A dermatoscopic image of a skin lesion:
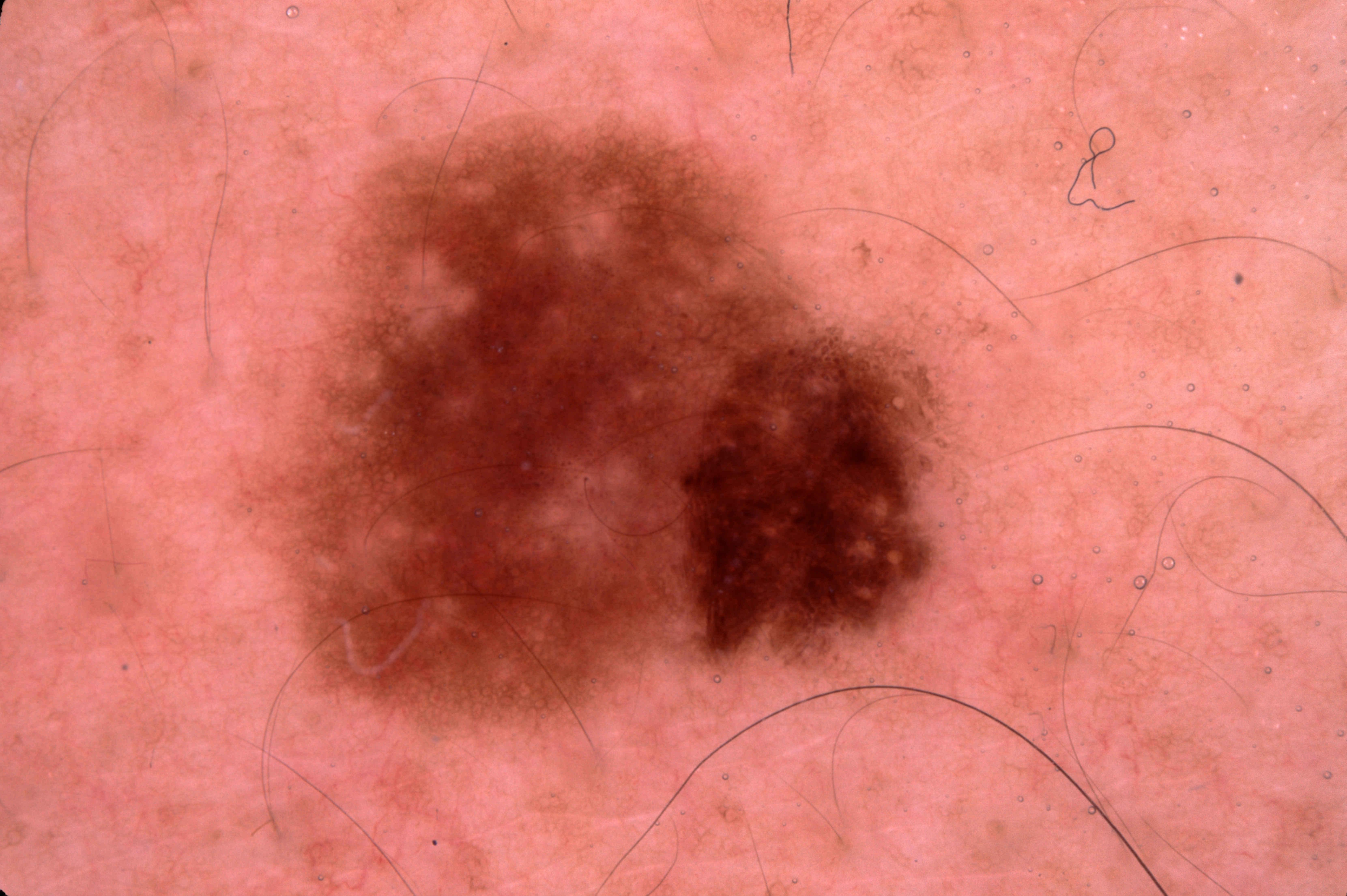lesion bbox = <bbox>238, 101, 973, 746</bbox>; diagnosis = a melanocytic nevus.